The lesion involves the leg, arm and front of the torso · the patient is 30–39, male · close-up view:
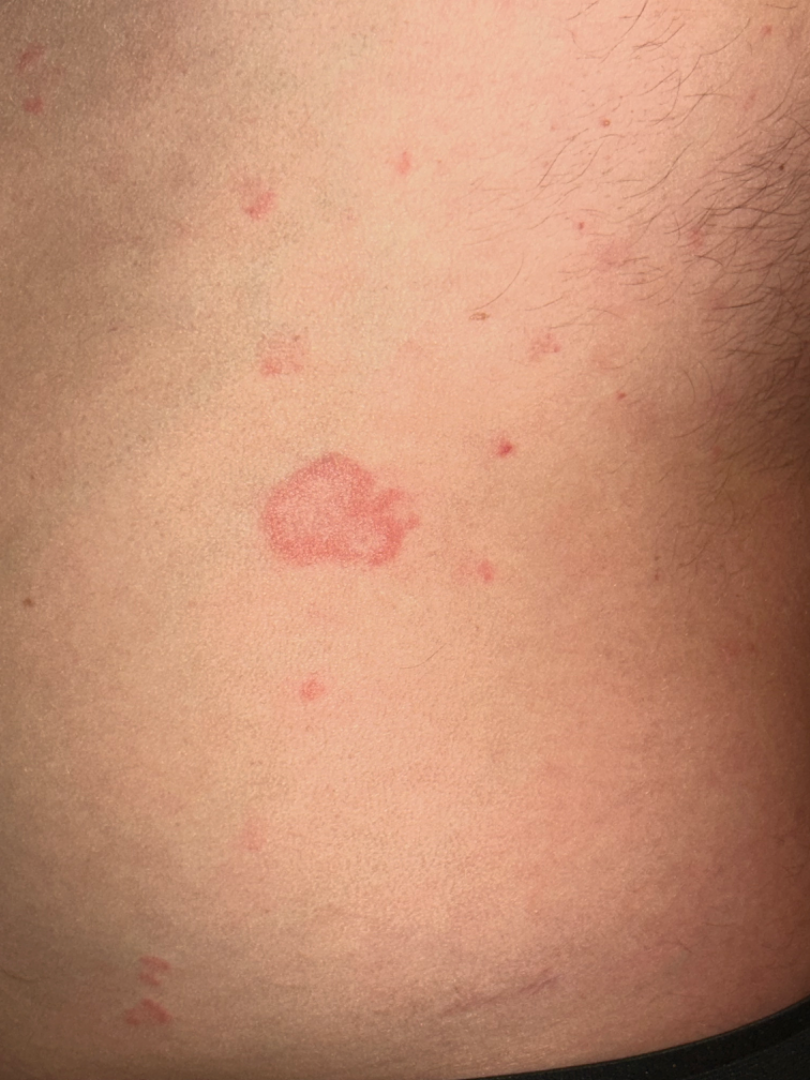Notes:
* impression — a single dermatologist reviewed the case: Pityriasis rosea, Psoriasis and Eczema were each considered, in no particular order